A dermoscopic image of a skin lesion:
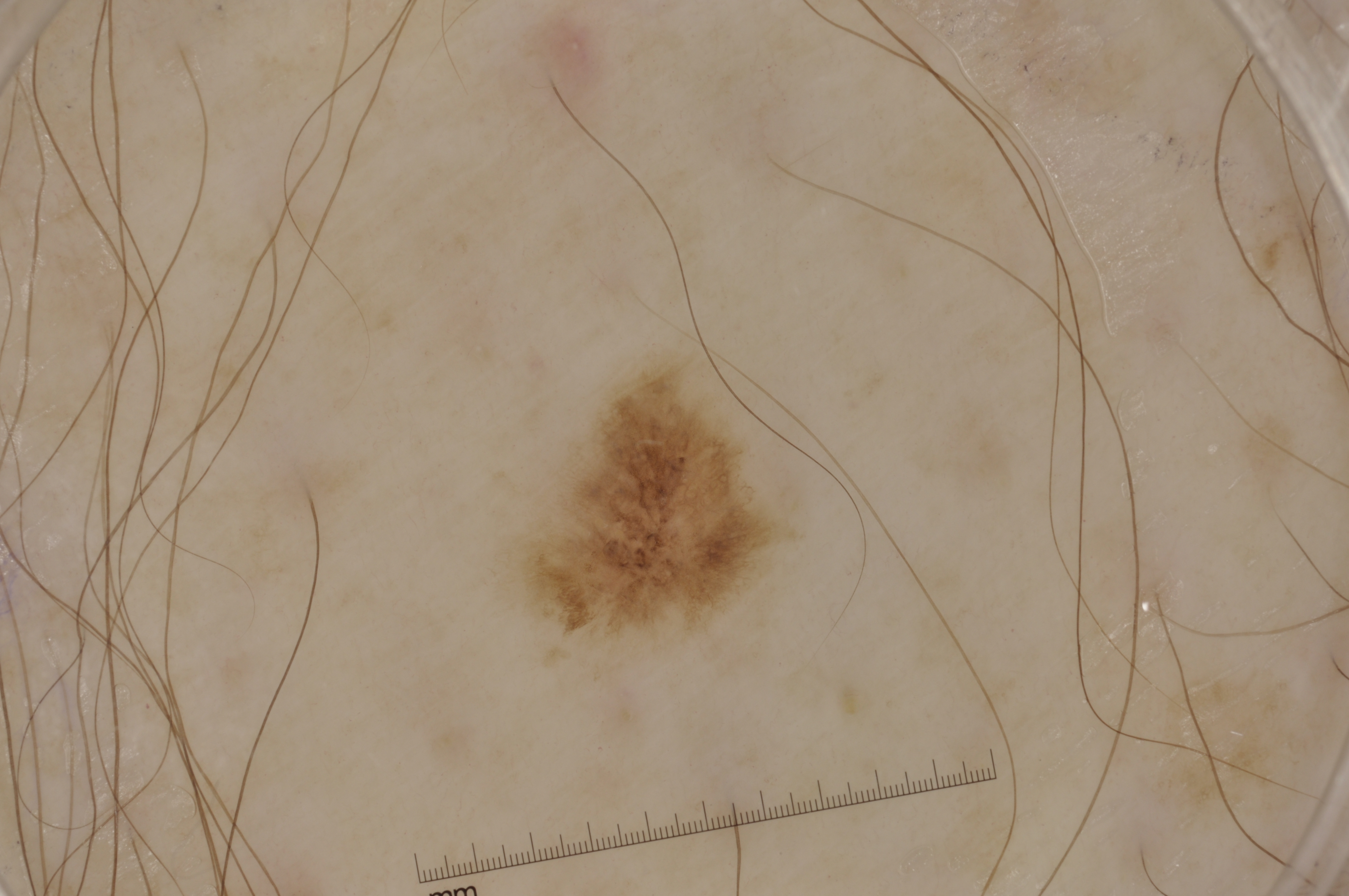Q: What is the lesion's bounding box?
A: box(517, 365, 780, 637)
Q: What is the diagnosis?
A: a melanocytic nevus, a benign lesion